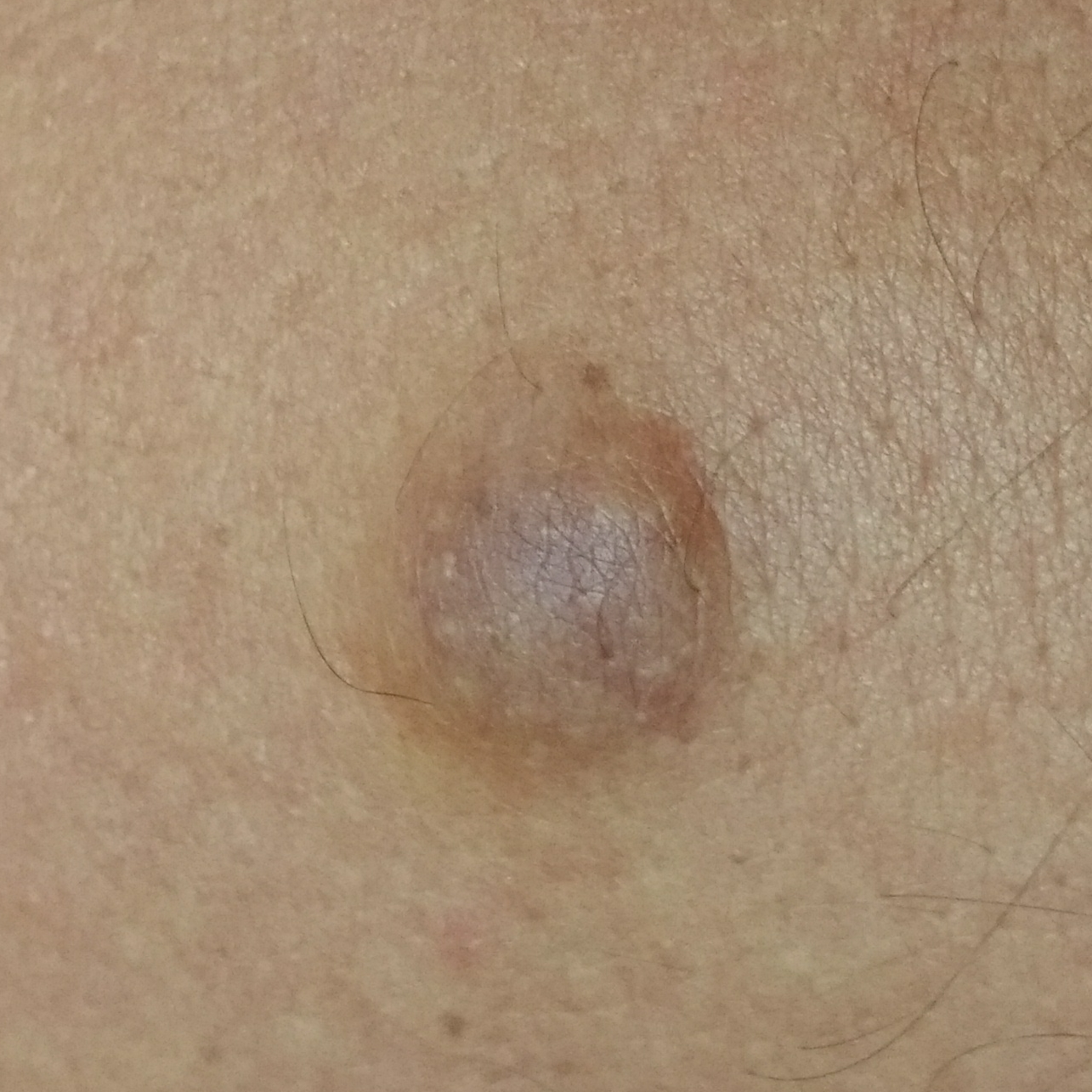Q: Where on the body is the lesion?
A: the back
Q: What does the patient describe?
A: elevation, growth / no bleeding
Q: What was the clinical impression?
A: nevus (clinical consensus)